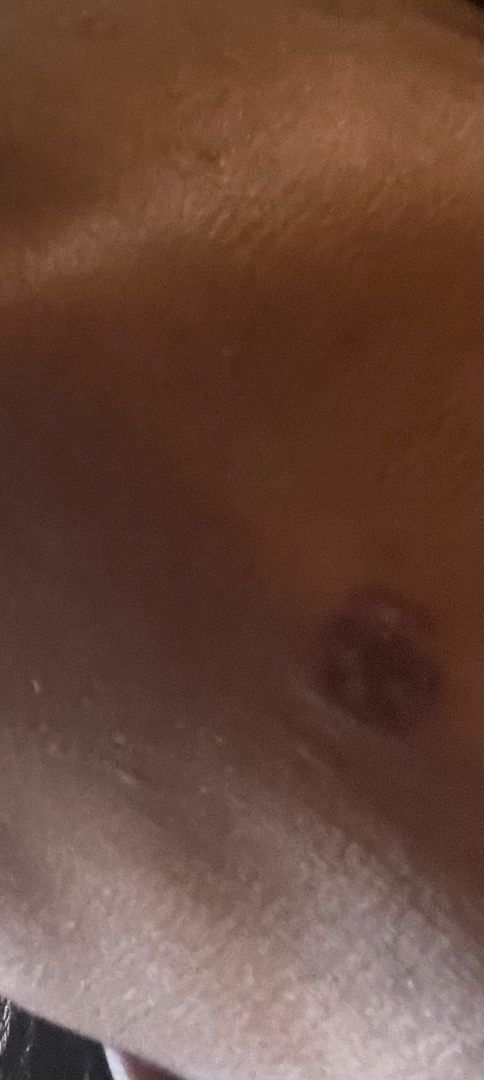assessment: ungradable on photographic review
patient: female, age 40–49
duration: one to four weeks
skin_tone:
  fitzpatrick: V
  monk_skin_tone:
    - 4
    - 7
shot_type: close-up
body_site: head or neck
patient_category: skin that appeared healthy to them
texture:
  - flat
  - rough or flaky
systemic_symptoms: none reported